The patient describes having a moderate number of moles. Acquired for a research image collection, with no referral diagnosis. A male patient 65 years old. A clinical close-up of a skin lesion. The patient reports a personal history of cancer. The patient says their skin tans without first burning — 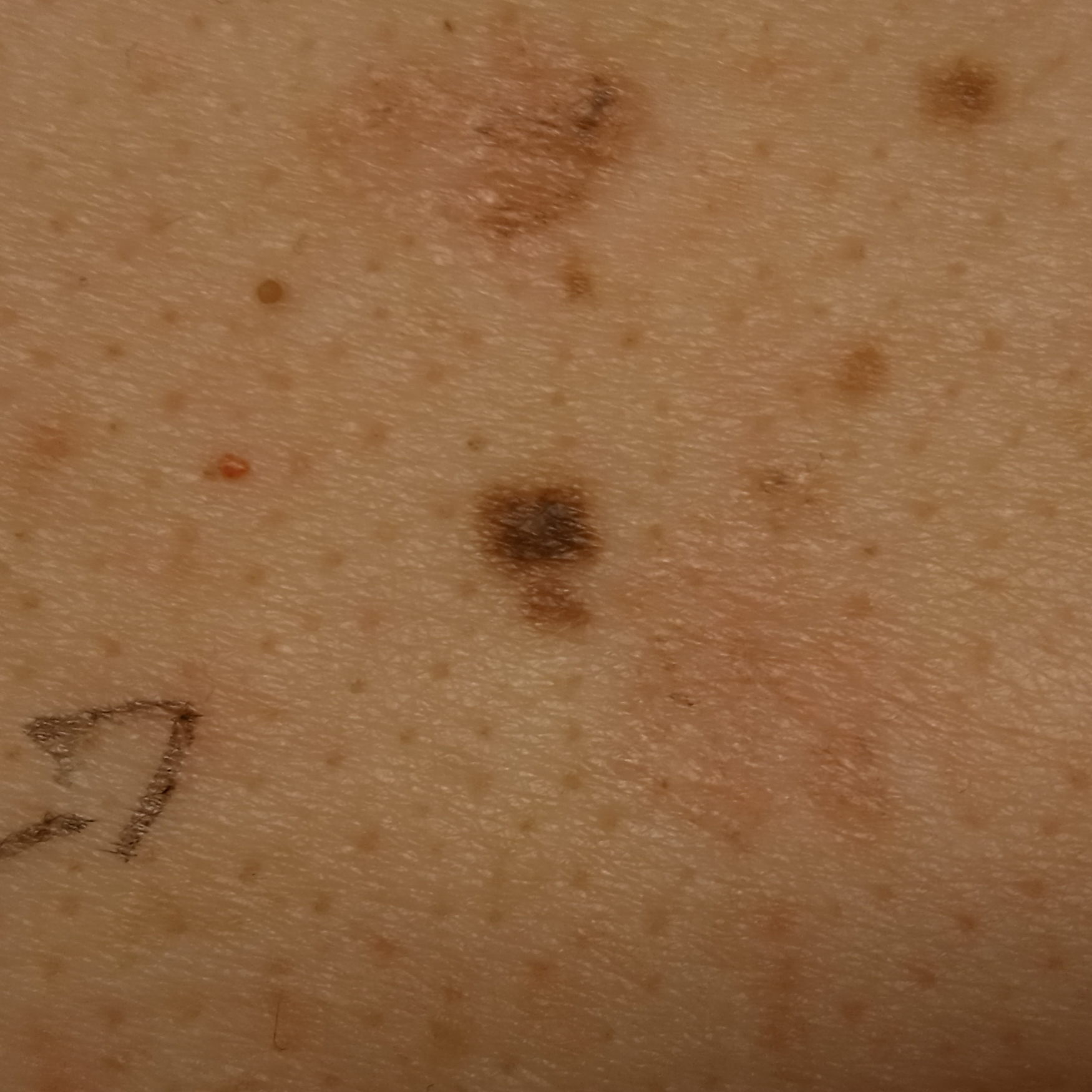{
  "lesion_size": {
    "diameter_mm": 4.2
  },
  "diagnosis": {
    "name": "atypical (dysplastic) nevus",
    "malignancy": "benign"
  }
}